Imaged for a research study, with no referral diagnosis recorded. A clinical photograph of a skin lesion. A male patient 83 years of age:
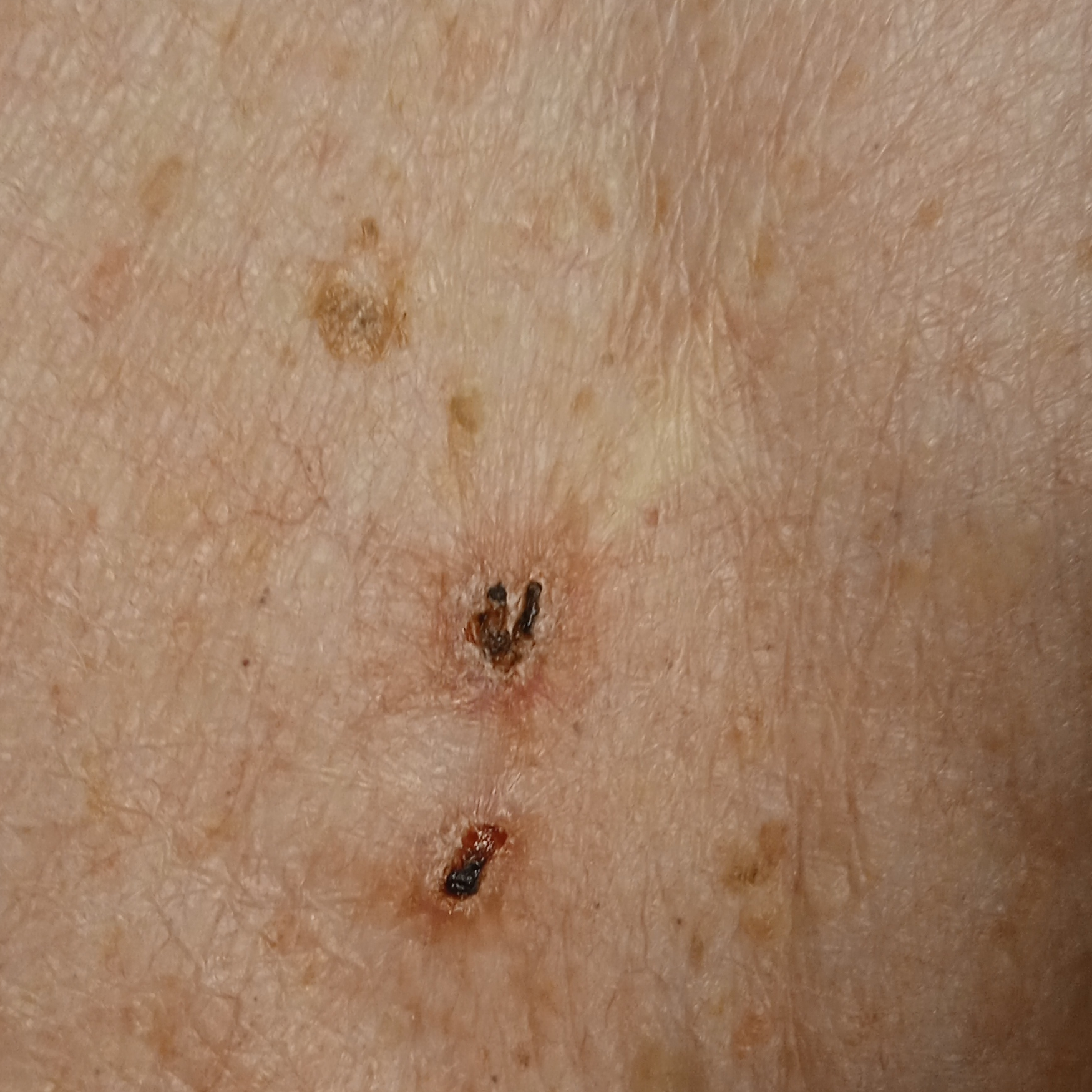Located on the back. The lesion measures approximately 9.5 mm. The consensus diagnosis for this lesion was a basal cell carcinoma.